Female contributor, age 50–59; associated systemic symptoms include joint pain; located on the leg; this is a close-up image; reported lesion symptoms include burning, pain and itching; the lesion is described as flat; reported duration is one to four weeks — 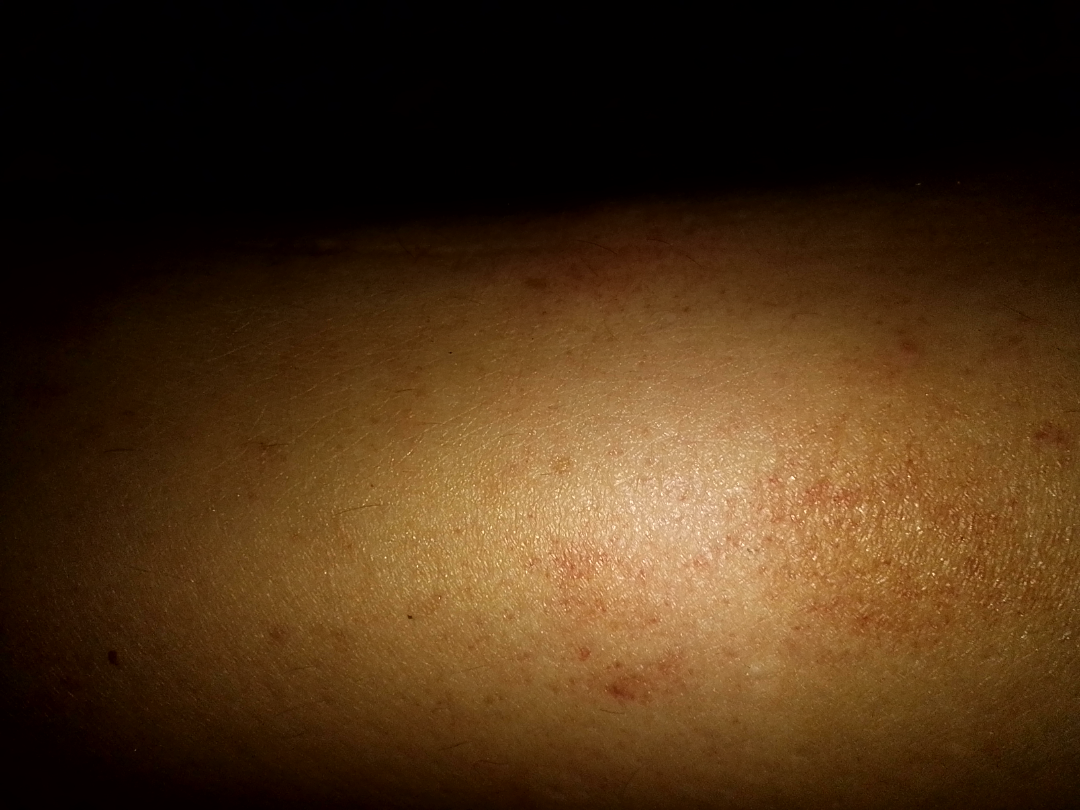Notes:
• dermatologist impression — in keeping with Pigmented purpuric eruption